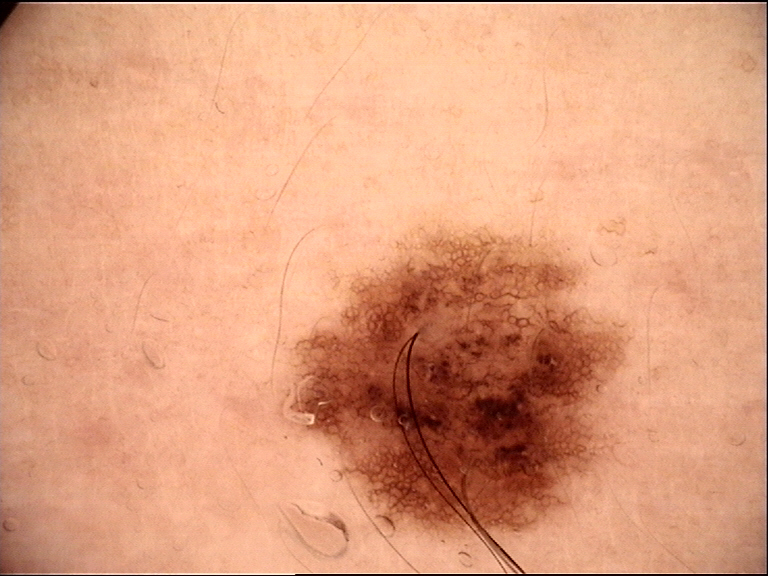The diagnosis was a benign lesion — a dysplastic compound nevus.